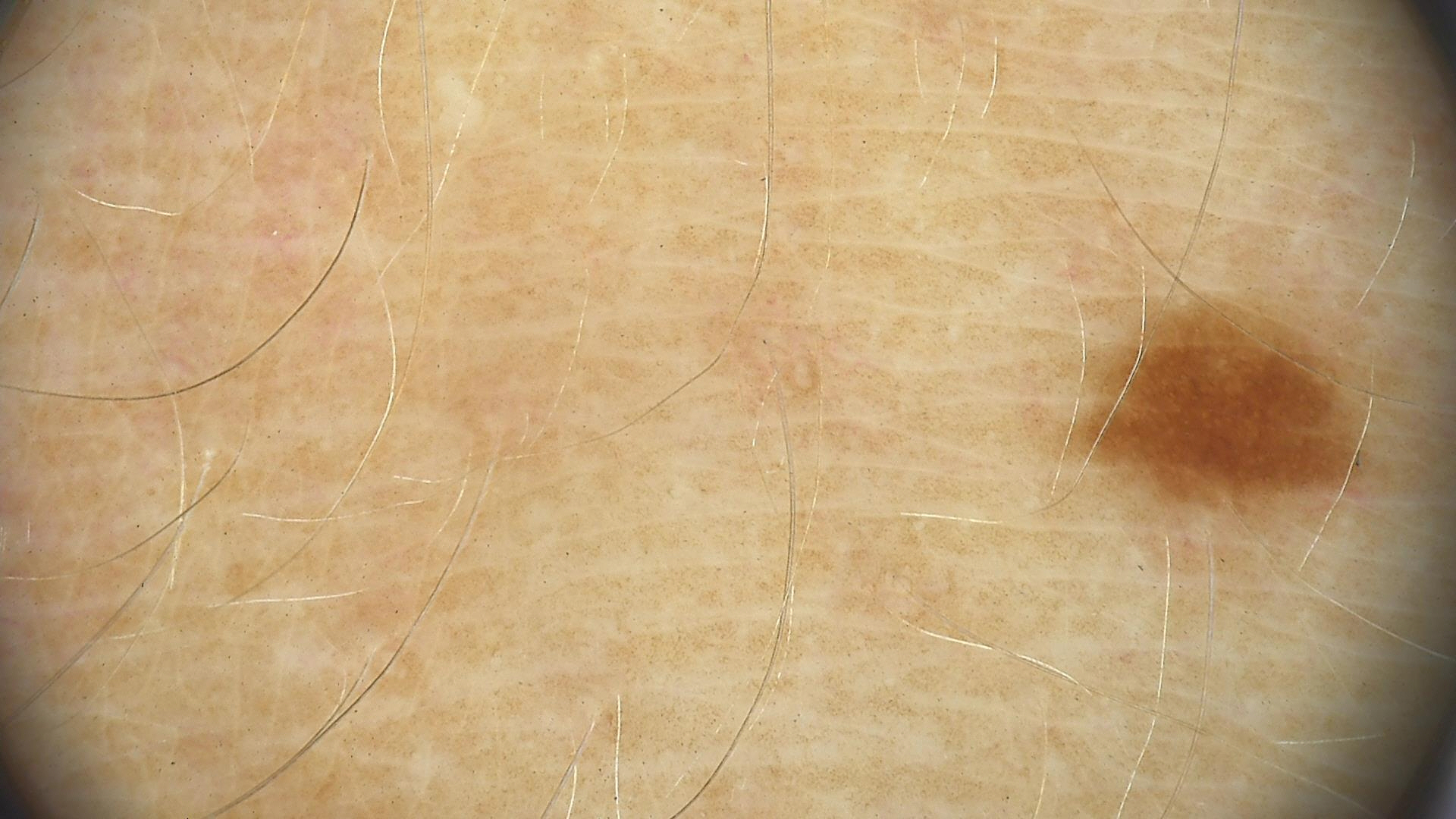<dermoscopy>
<image>dermatoscopy</image>
<lesion_type>
<main_class>banal</main_class>
<pattern>junctional</pattern>
</lesion_type>
<diagnosis>
<name>junctional nevus</name>
<code>jb</code>
<malignancy>benign</malignancy>
<super_class>melanocytic</super_class>
<confirmation>expert consensus</confirmation>
</diagnosis>
</dermoscopy>